Dermoscopy of a skin lesion.
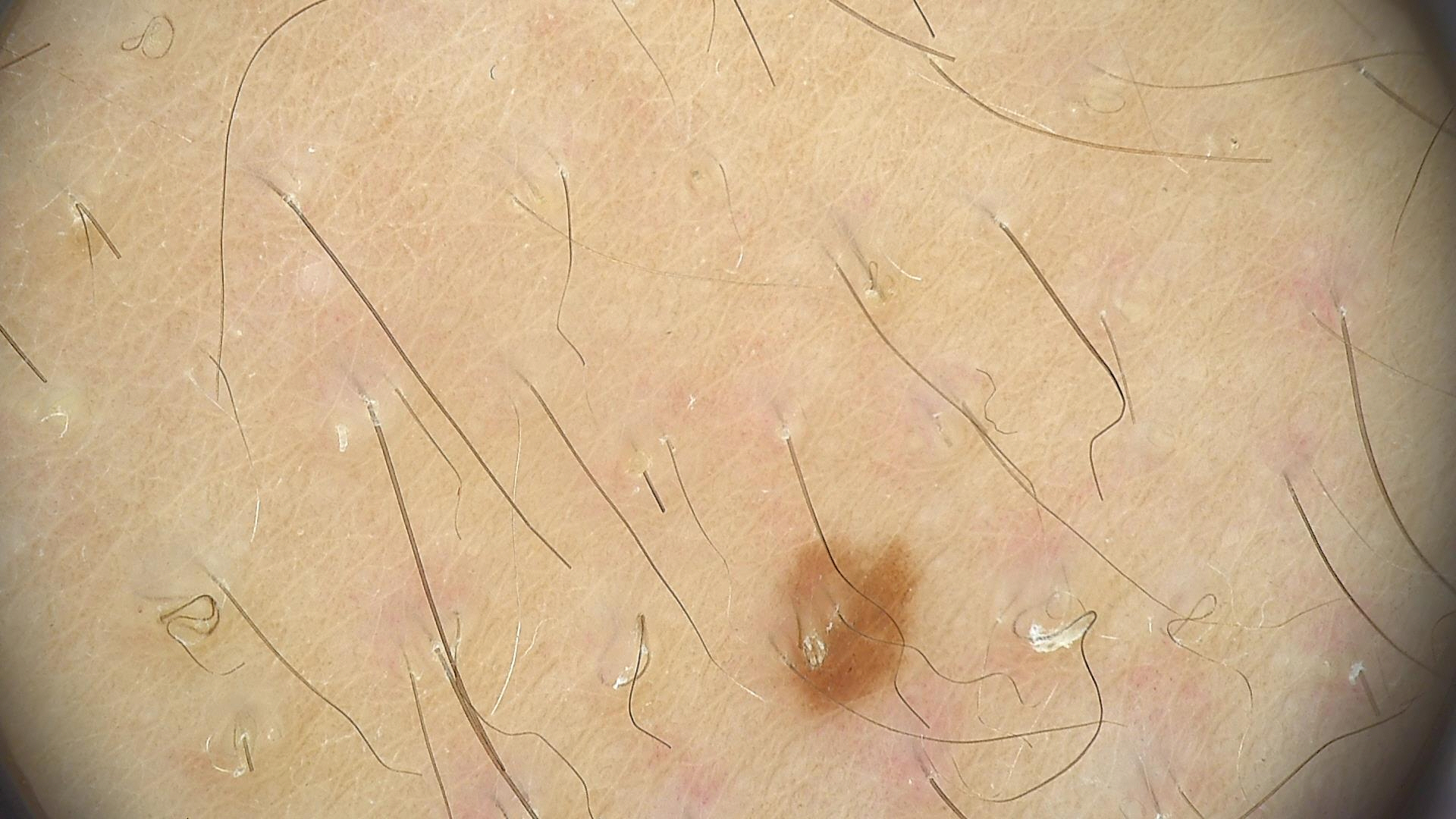lesion type: banal; label: junctional nevus (expert consensus).